A male subject age 83 · a dermoscopy image of a skin lesion — 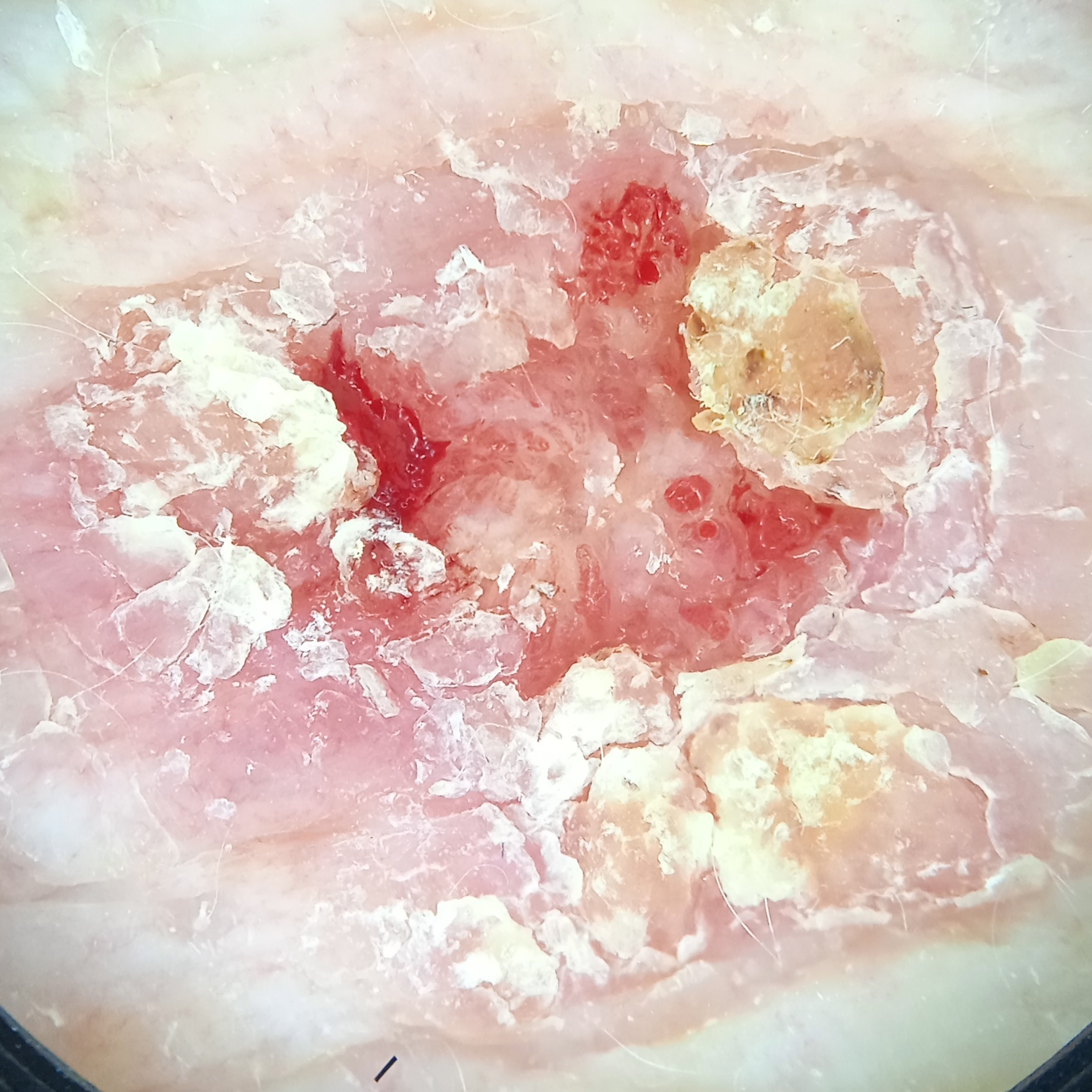Impression: The dermatologists' assessment was a squamous cell carcinoma.